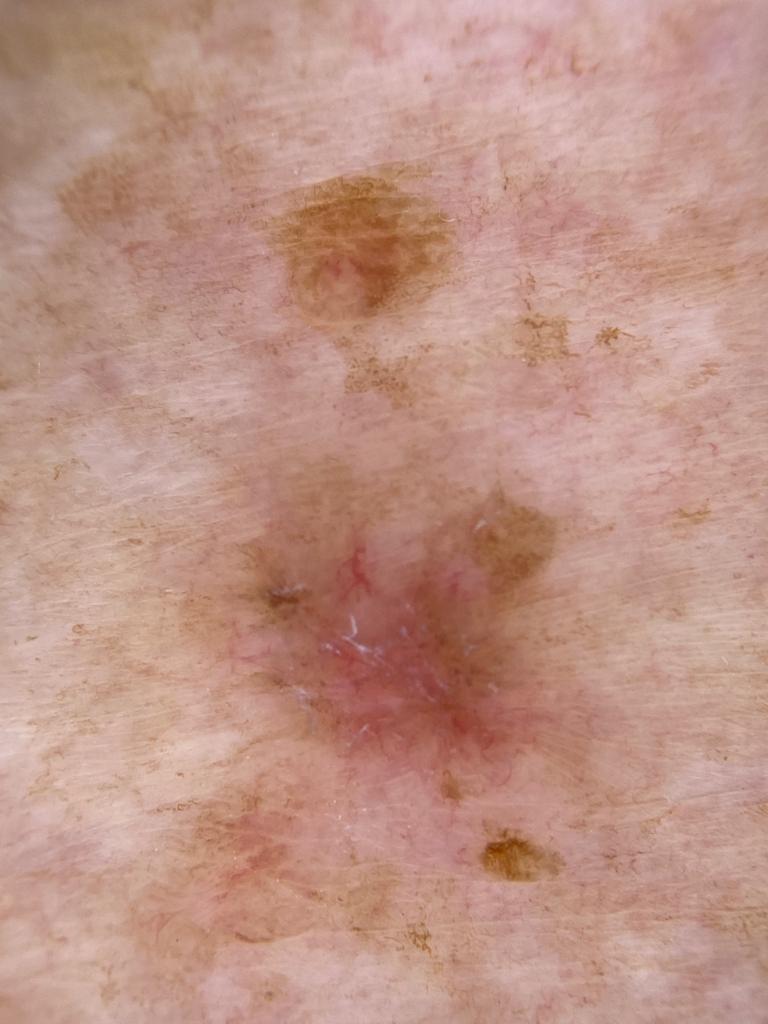The chart records no previous melanoma and no first-degree relative with melanoma.
Fitzpatrick II.
A contact-polarized dermoscopy image of a skin lesion.
A female subject aged 68-72.
The lesion is on the trunk (the anterior trunk).
On biopsy, the diagnosis was a malignant lesion — a basal cell carcinoma.